A dermoscopic image of a skin lesion: 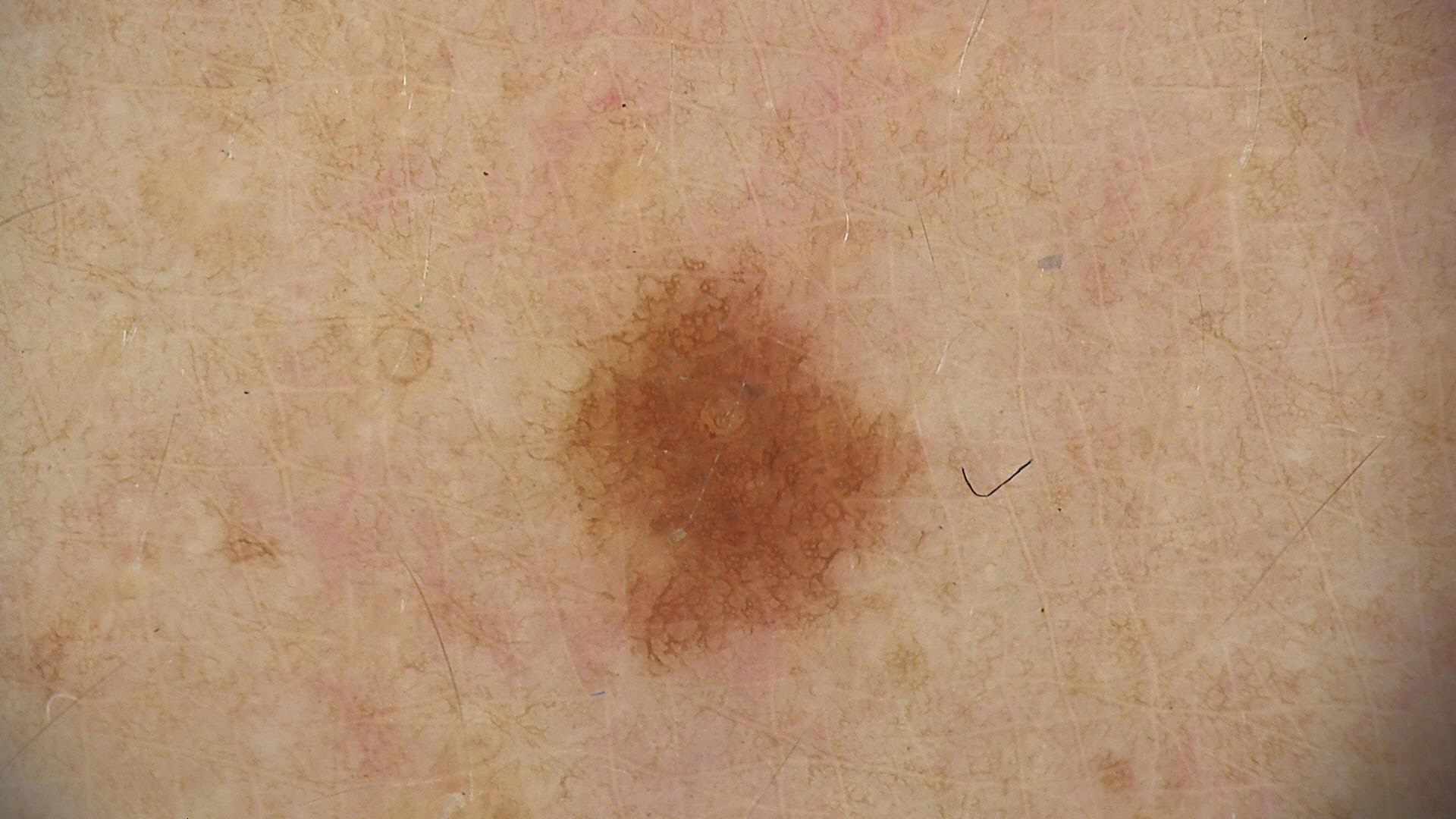Consistent with a dysplastic junctional nevus.